A skin lesion imaged with a dermatoscope.
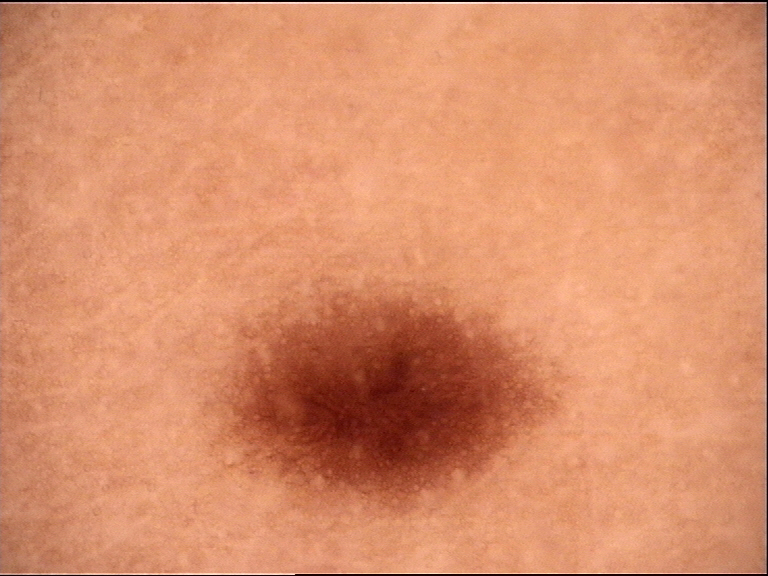Impression: Classified as a banal lesion — a junctional nevus.